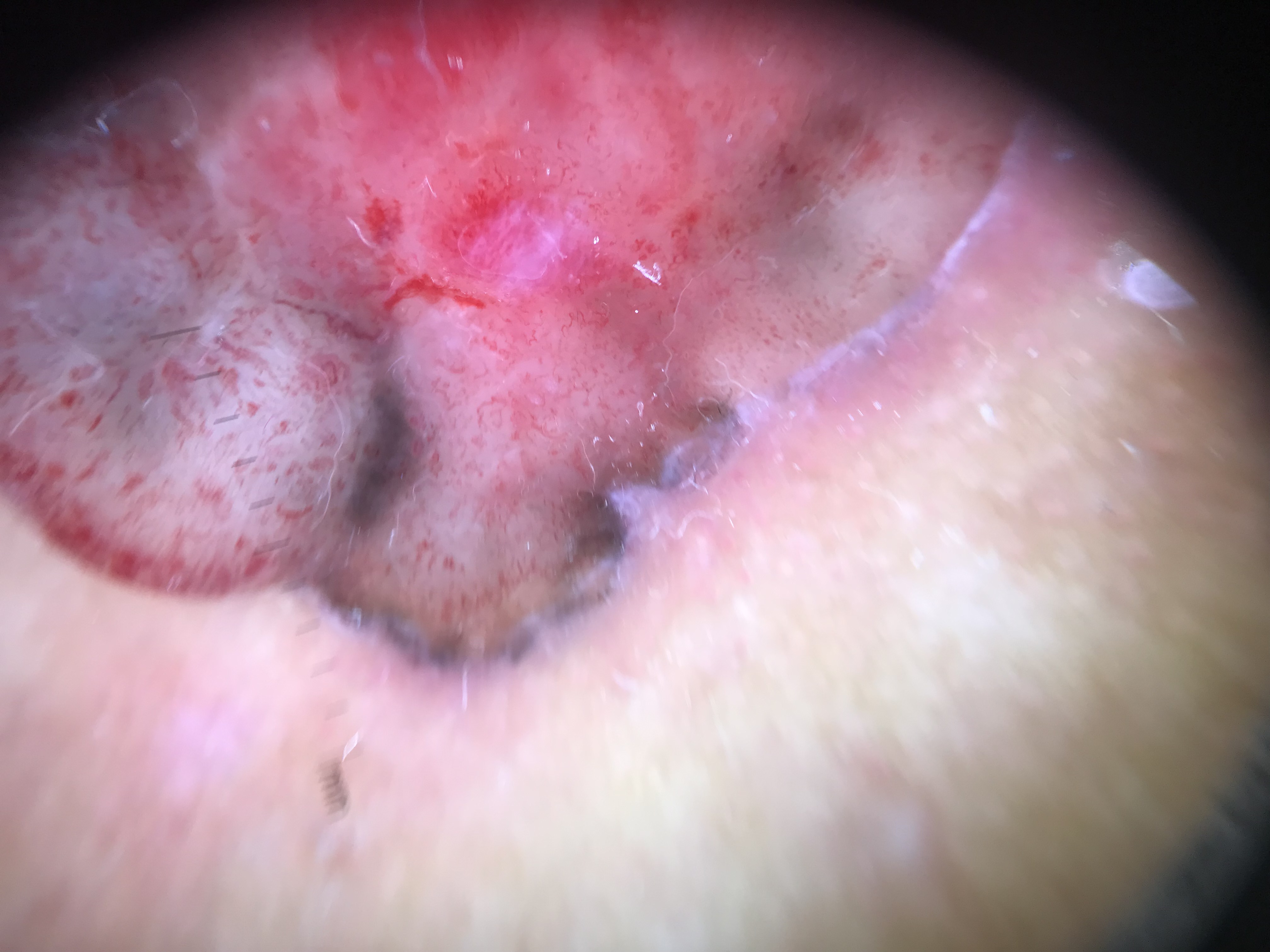A dermoscopic close-up of a skin lesion.
The morphology is that of a keratinocytic lesion.
Biopsy-confirmed as a basal cell carcinoma.